The affected area is the leg and arm, this is a close-up image.
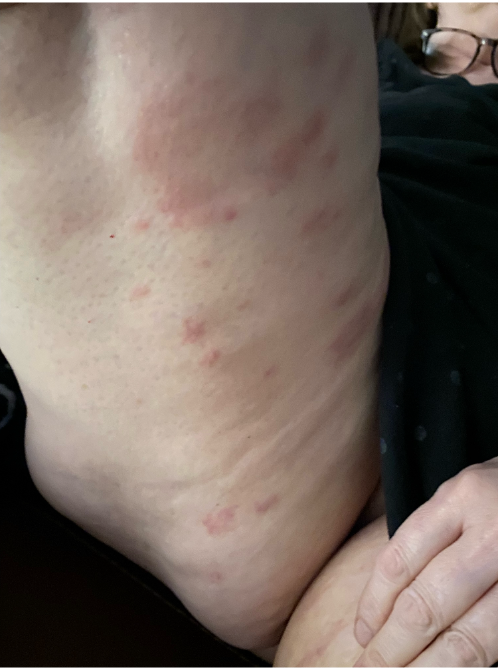Review:
Single-reviewer assessment: Cutaneous T Cell Lymphoma, Granuloma annulare and Eczema were considered with similar weight.